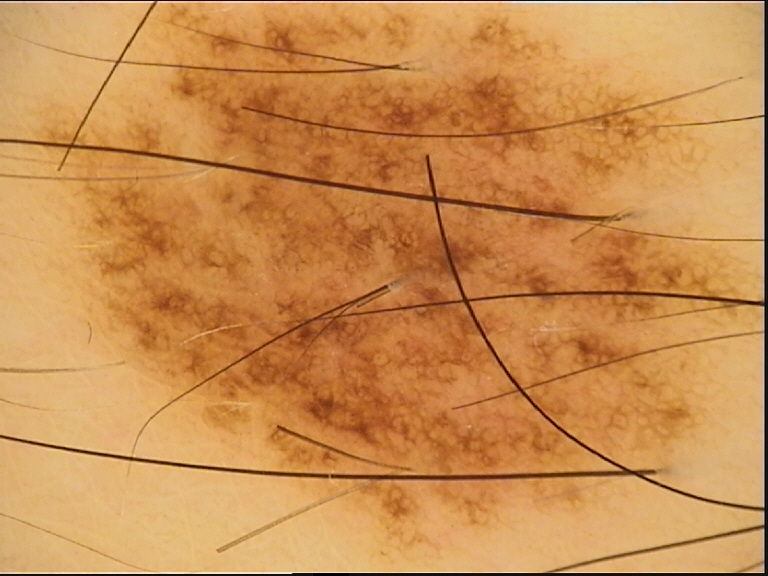Case:
* diagnosis: dysplastic junctional nevus (expert consensus)